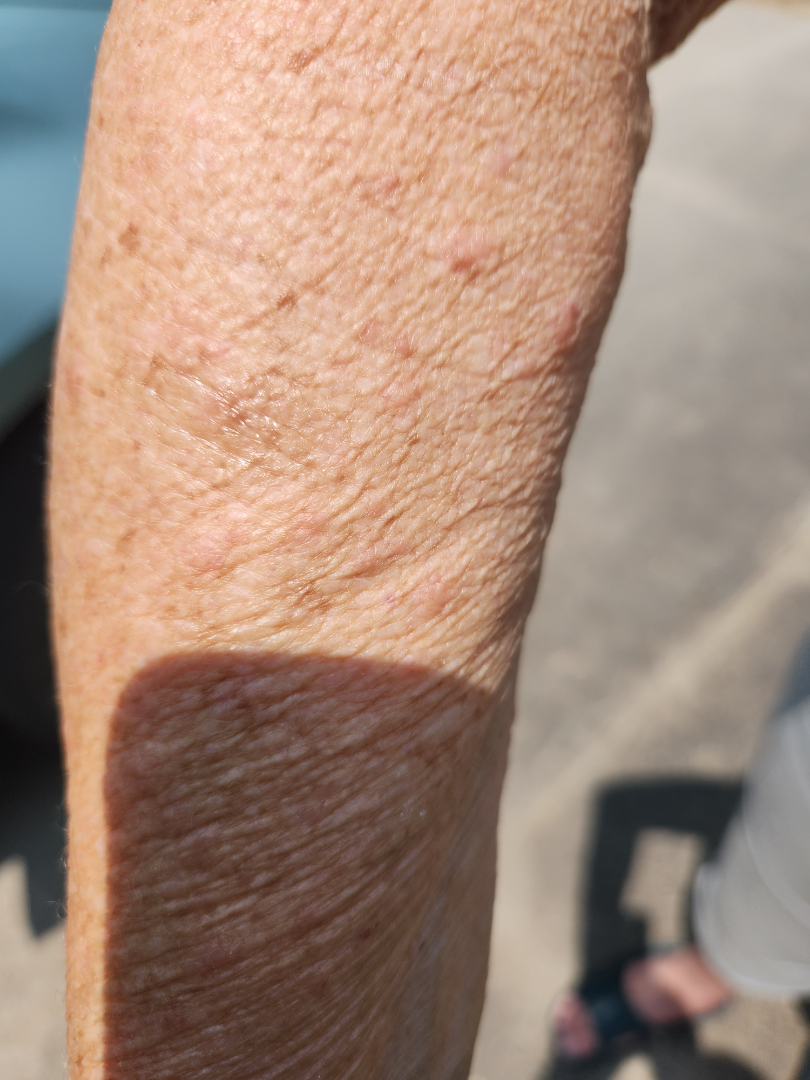Q: Could the case be diagnosed?
A: unable to determine
Q: When did this start?
A: less than one week
Q: Any systemic symptoms?
A: none reported
Q: How does the patient describe it?
A: a rash
Q: Image view?
A: close-up
Q: What symptoms does the patient report?
A: none reported
Q: Where on the body?
A: leg, head or neck and arm
Q: Patient demographics?
A: female, age 70–79